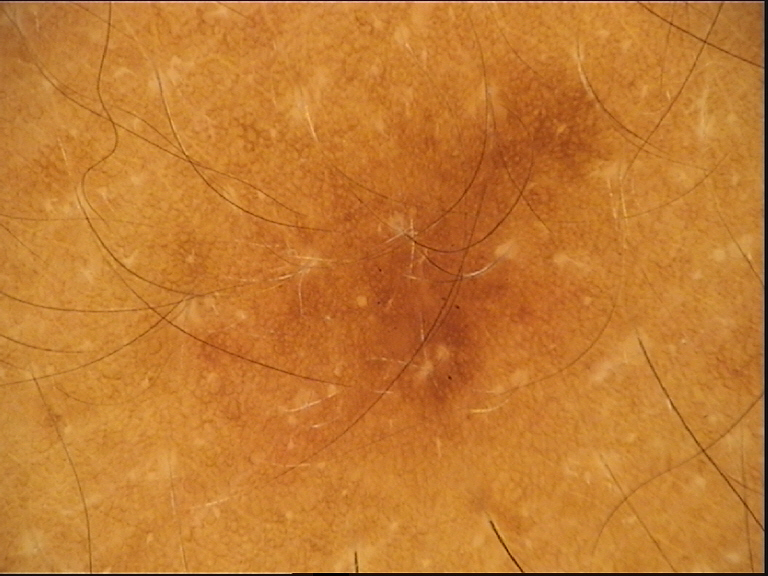image type=dermoscopy | category=fibro-histiocytic | assessment=dermatofibroma (expert consensus).